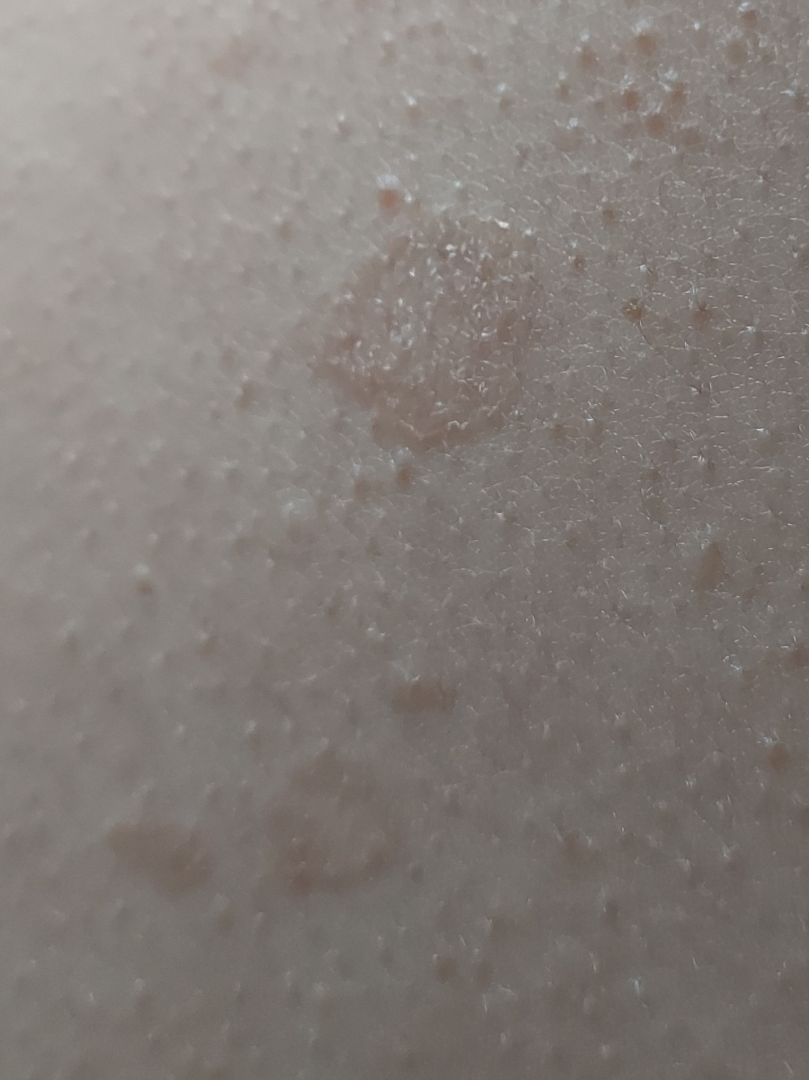Findings:
– diagnostic considerations: most consistent with Tinea Versicolor